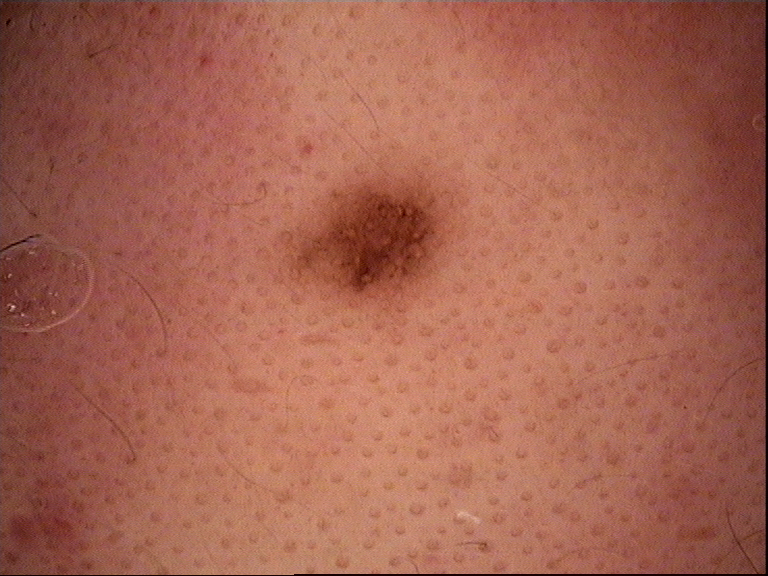Findings:
- imaging · dermatoscopy
- diagnosis · dysplastic junctional nevus (expert consensus)